Dermoscopy of a skin lesion: 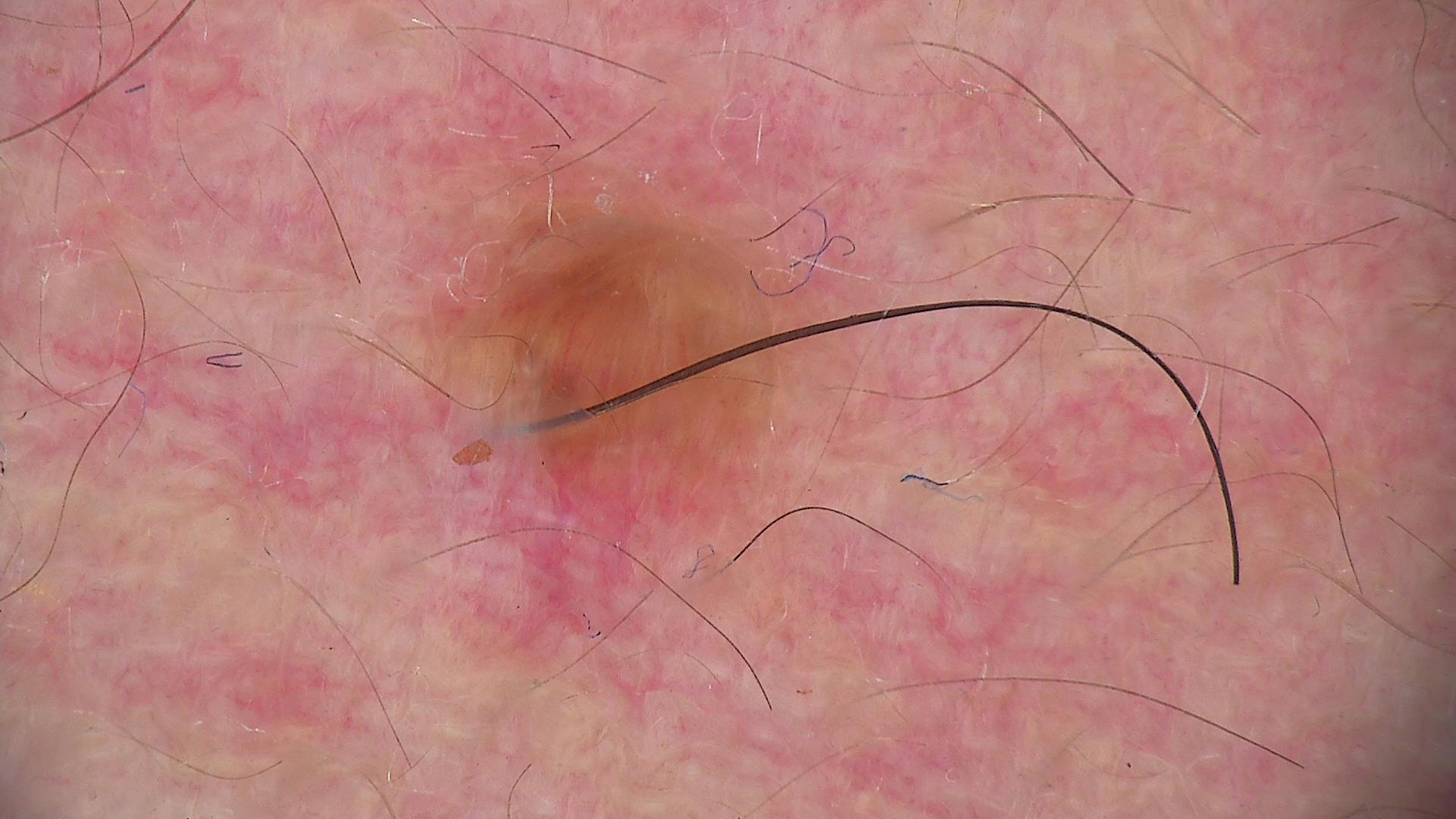<lesion>
  <lesion_type>
    <main_class>banal</main_class>
    <pattern>dermal</pattern>
  </lesion_type>
  <diagnosis>
    <name>dermal nevus</name>
    <code>db</code>
    <malignancy>benign</malignancy>
    <super_class>melanocytic</super_class>
    <confirmation>expert consensus</confirmation>
  </diagnosis>
</lesion>